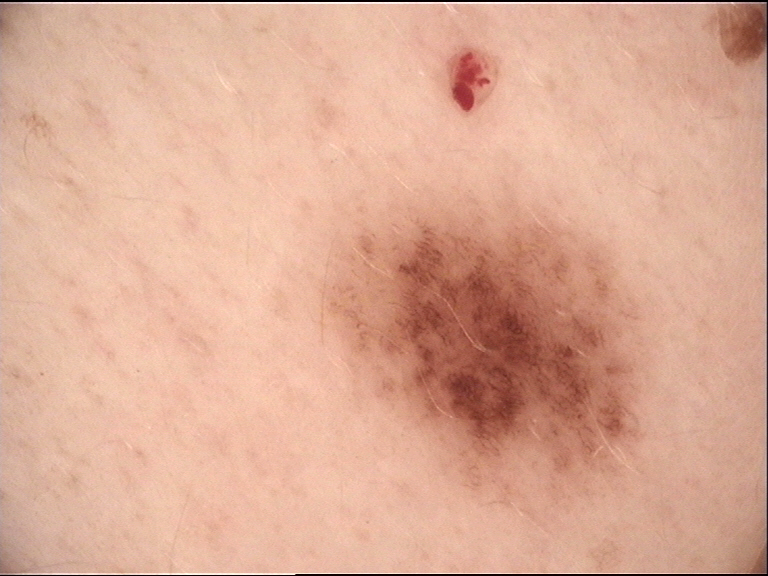Case:
• class: dysplastic junctional nevus (expert consensus)